A skin lesion imaged with a dermatoscope.
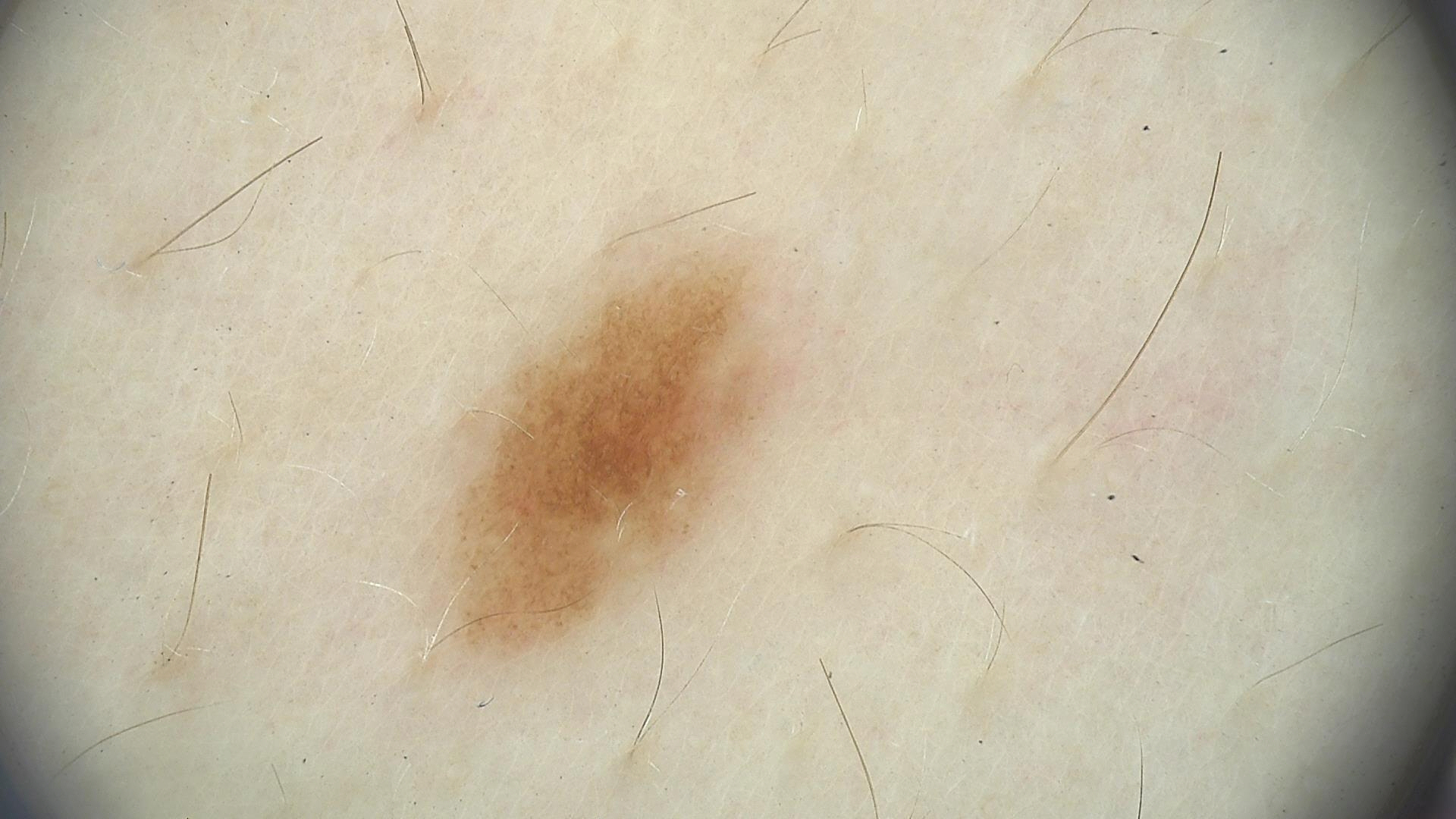| feature | finding |
|---|---|
| class | dysplastic junctional nevus (expert consensus) |